A male subject 54 years old; a clinical close-up photograph of a skin lesion:
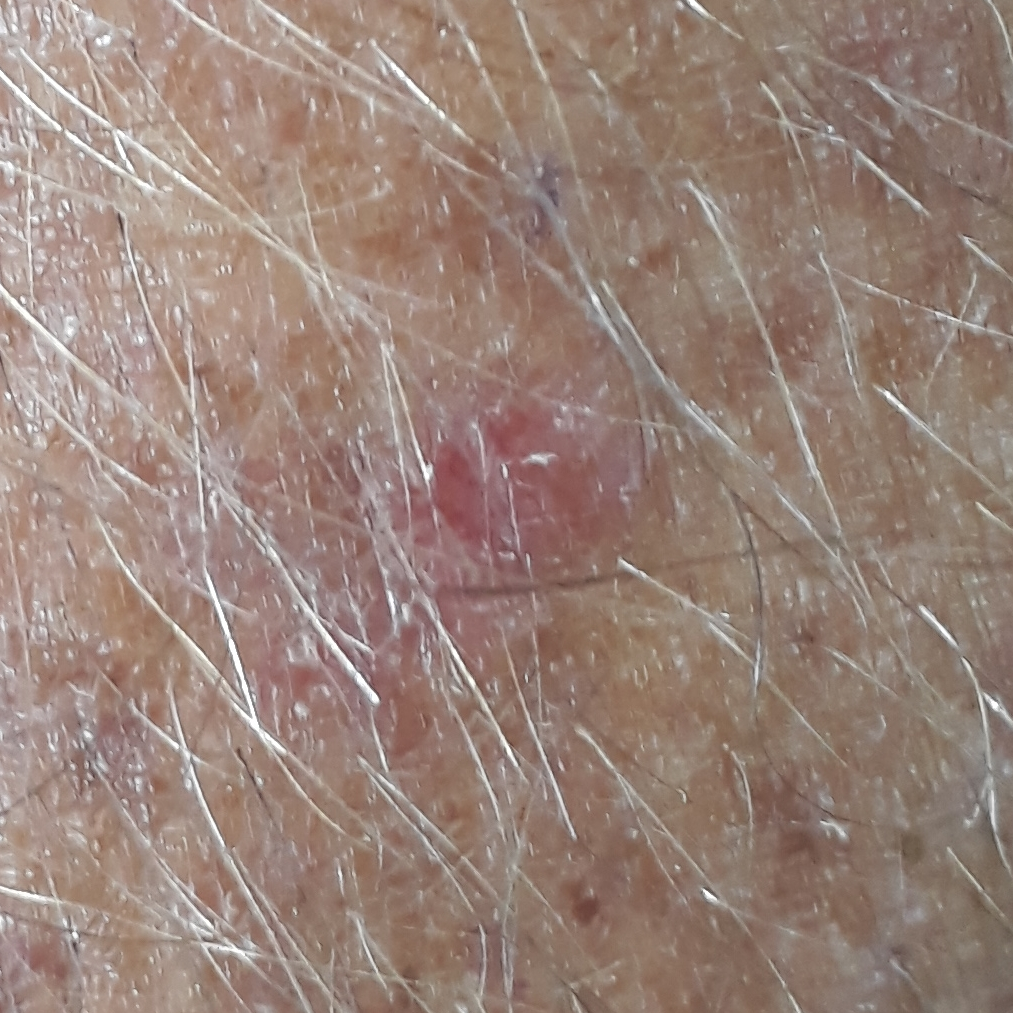Notes:
• location — a forearm
• patient-reported symptoms — elevation / no pain, no bleeding
• pathology — basal cell carcinoma (biopsy-proven)